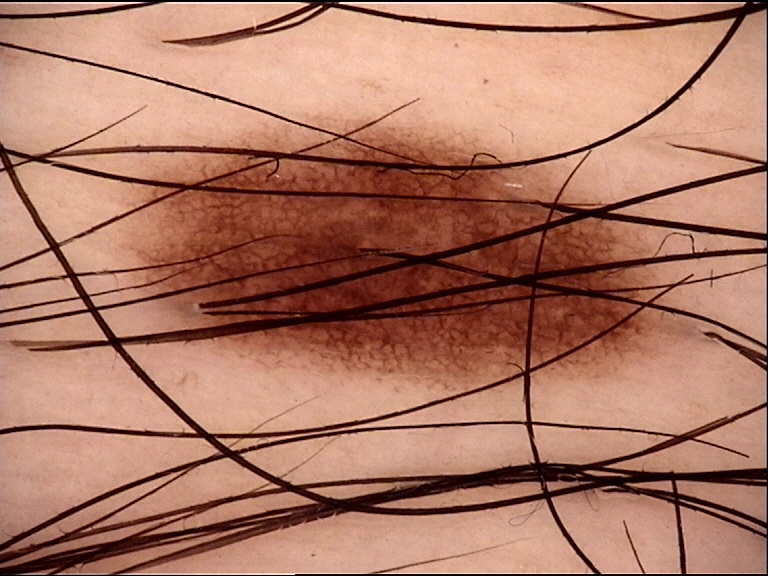A dermoscopic photograph of a skin lesion. Consistent with a dysplastic junctional nevus.